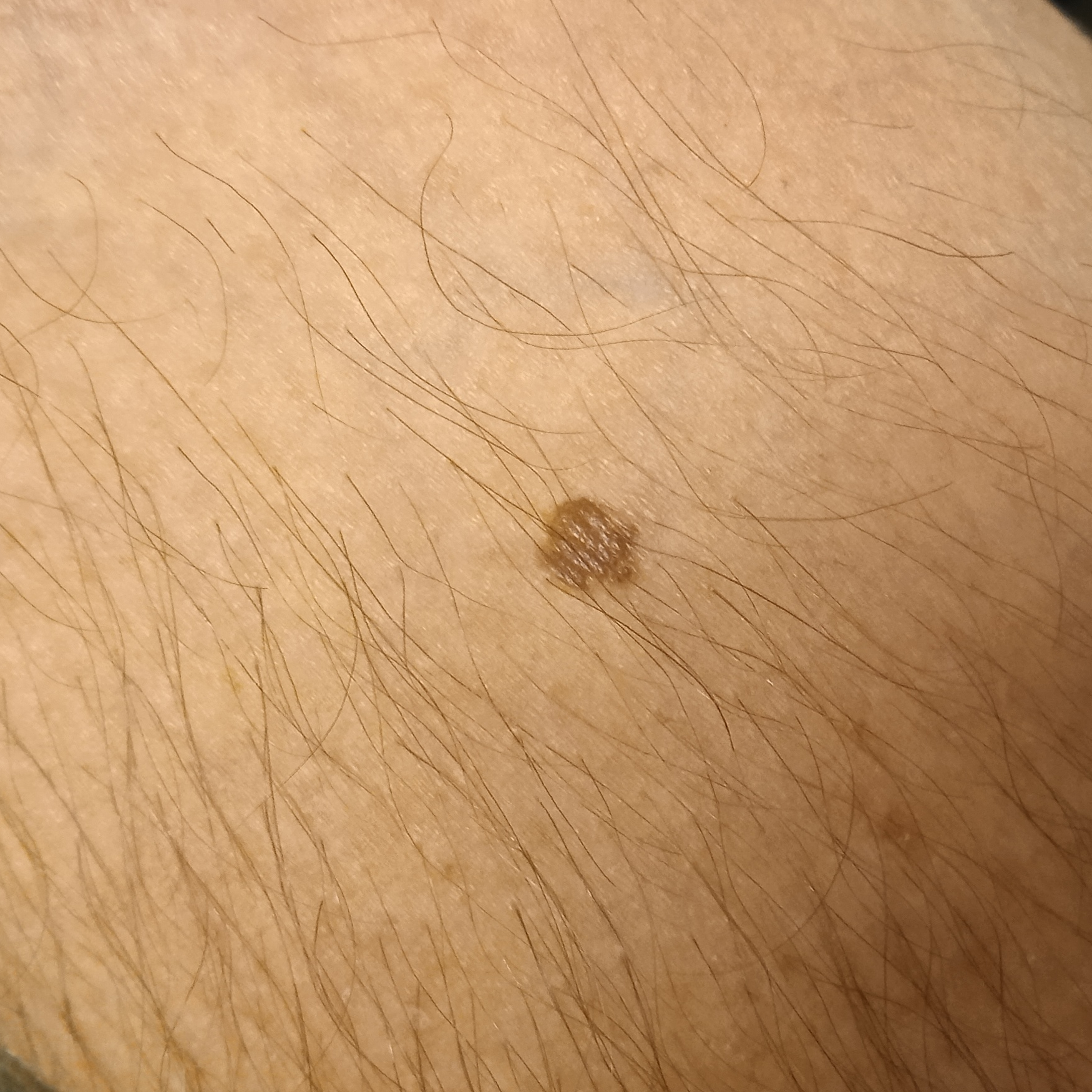Acquired for a research image collection, with no referral diagnosis. By self-report, a family history of skin cancer, immunosuppression, and a personal history of skin cancer. The patient says their skin reddens painfully with sun exposure. A macroscopic clinical photograph of a skin lesion. A male subject 65 years of age. Located on an arm. Measuring roughly 5.5 mm. The consensus diagnosis for this lesion was a melanocytic nevus.